A dermatoscopic image of a skin lesion:
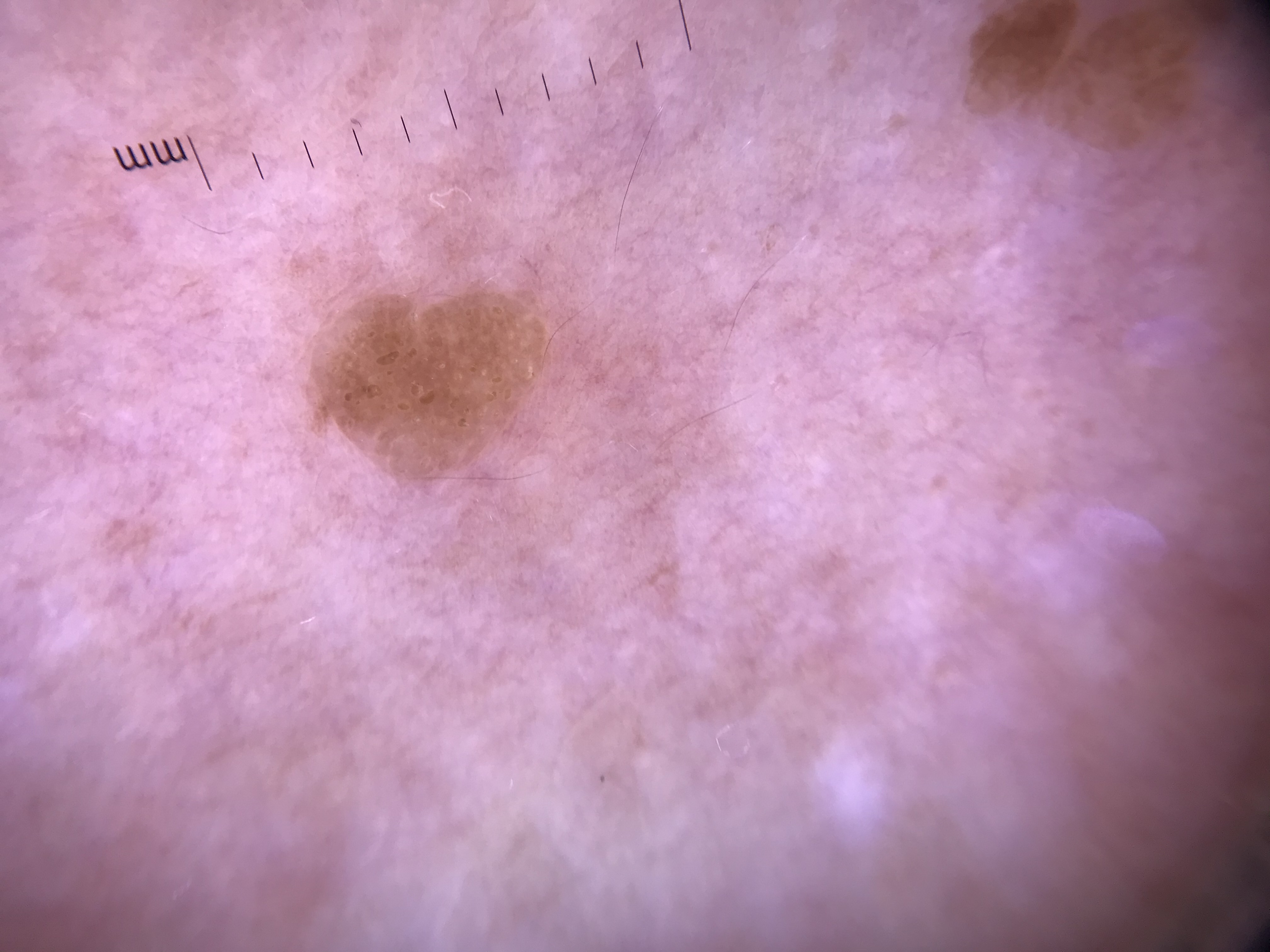Findings: The morphology is that of a keratinocytic lesion. Conclusion: Classified as a benign lesion — a seborrheic keratosis.